The patient reports bothersome appearance · the photograph is a close-up of the affected area · self-categorized by the patient as a pigmentary problem · the arm is involved · the subject is a female aged 40–49 · the patient reports the lesion is raised or bumpy · present for less than one week — 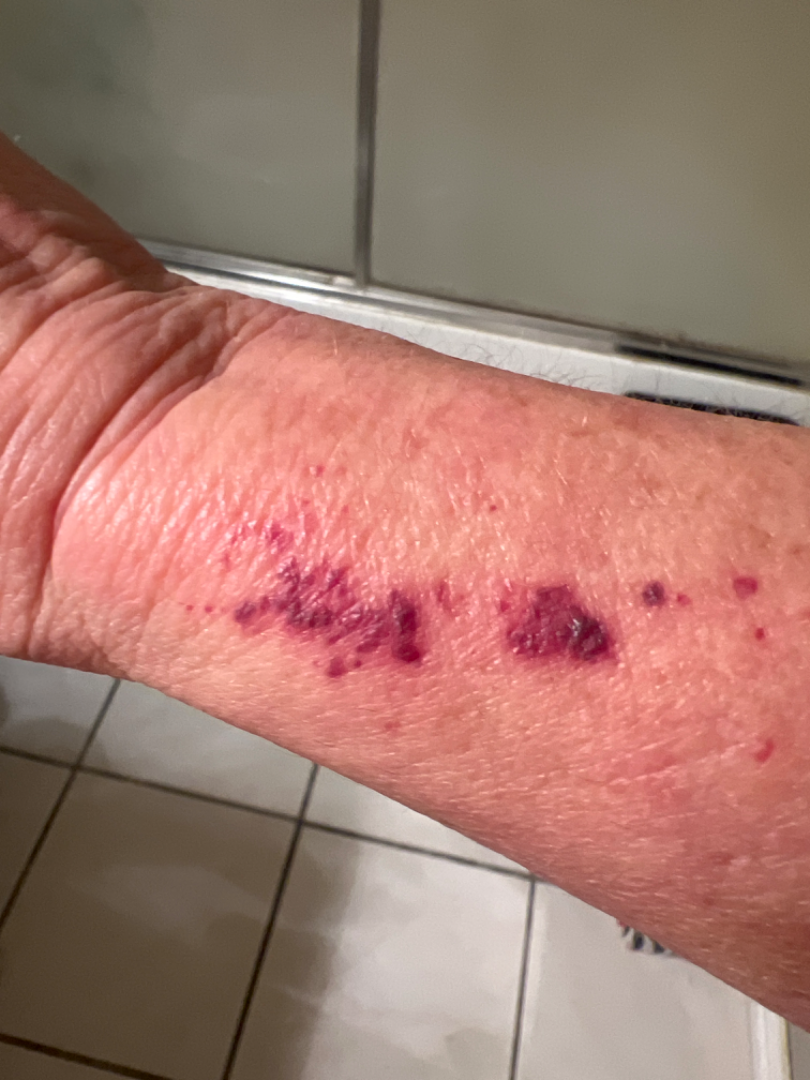Findings:
* assessment: unable to determine